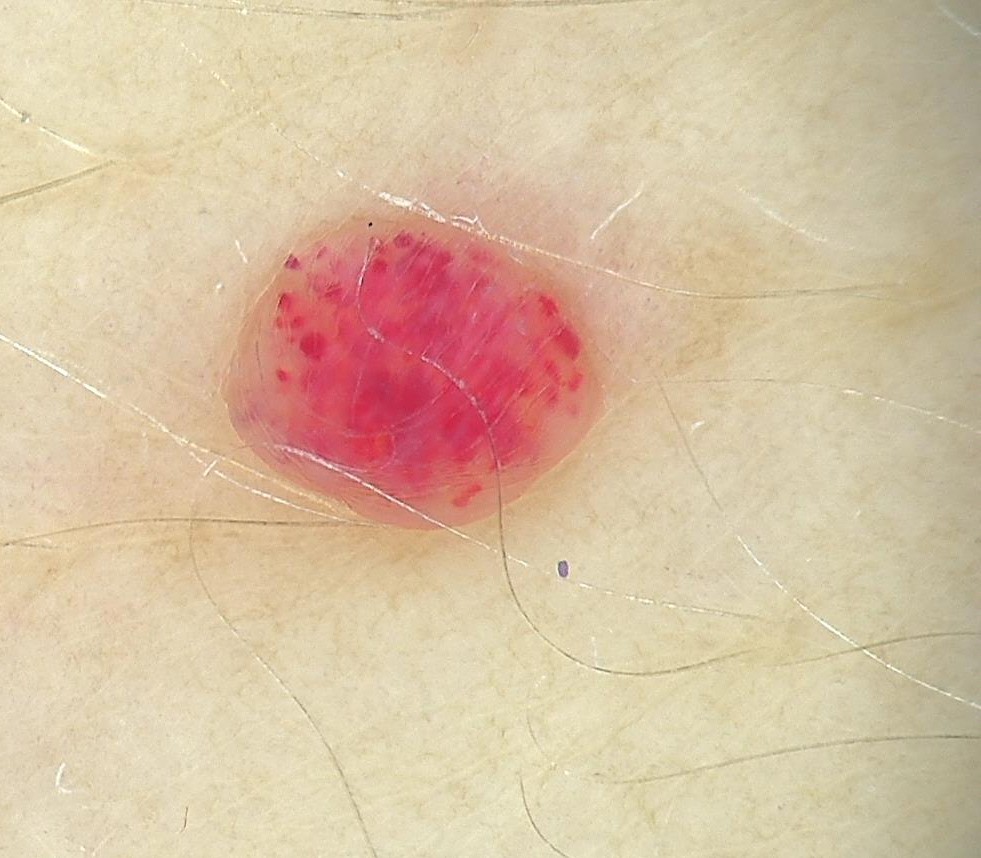Conclusion: Consistent with a hemangioma.